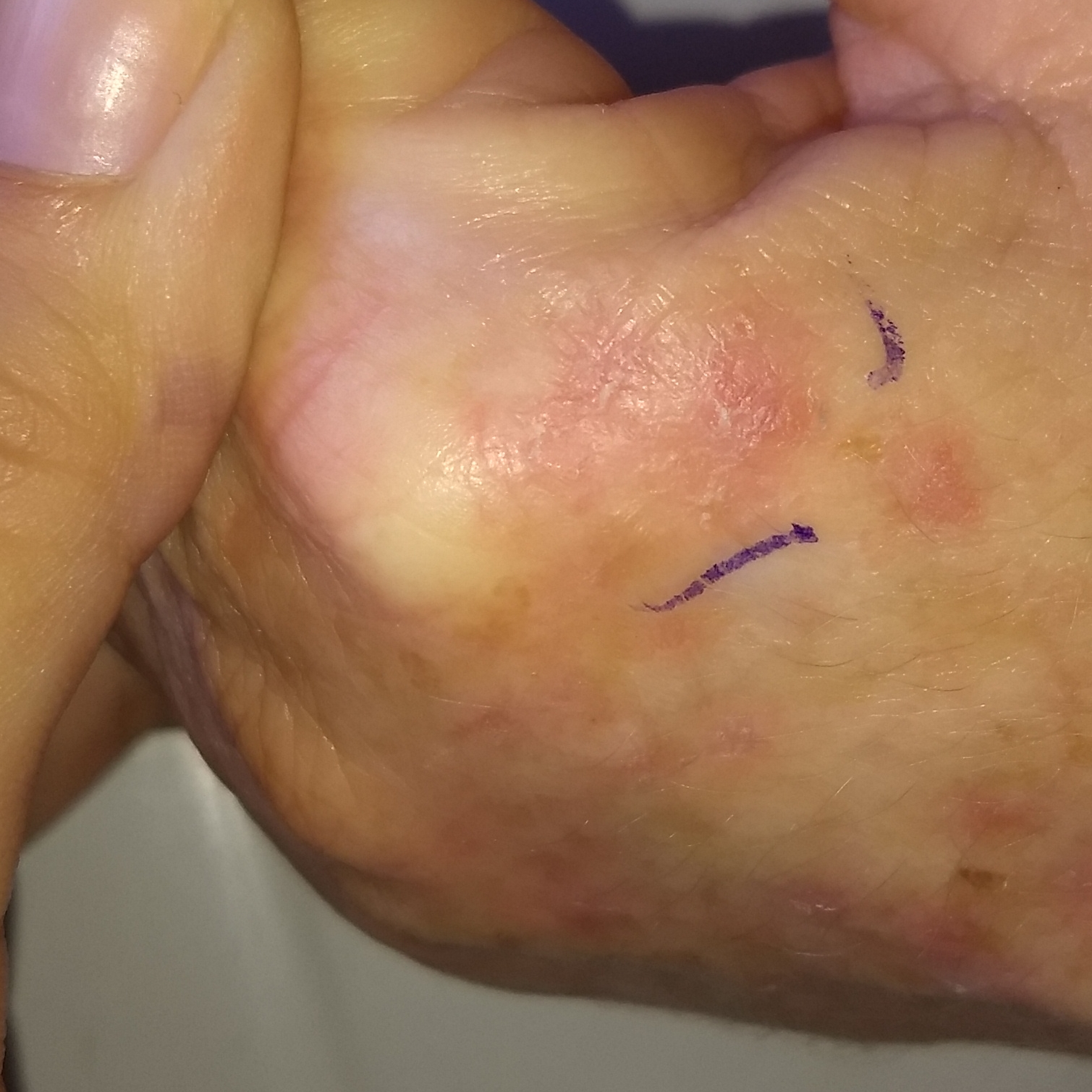Notes:
* image: clinical photograph
* risk factors: prior skin cancer (patient or family)
* subject: female, 51 years old
* region: a hand
* lesion size: approx. 25 × 11 mm
* reported symptoms: itching / no bleeding
* impression: actinic keratosis (clinical consensus)